The photo was captured at a distance — 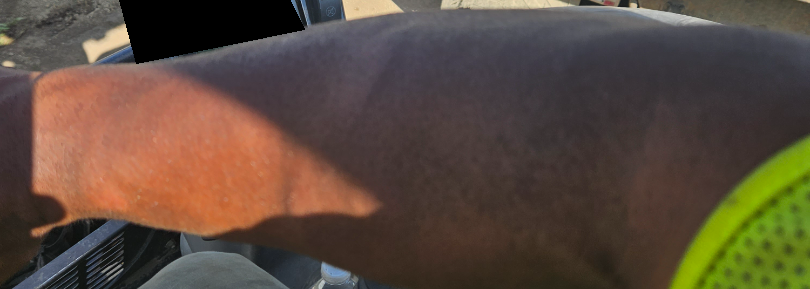Q: What was the assessment?
A: unable to determine